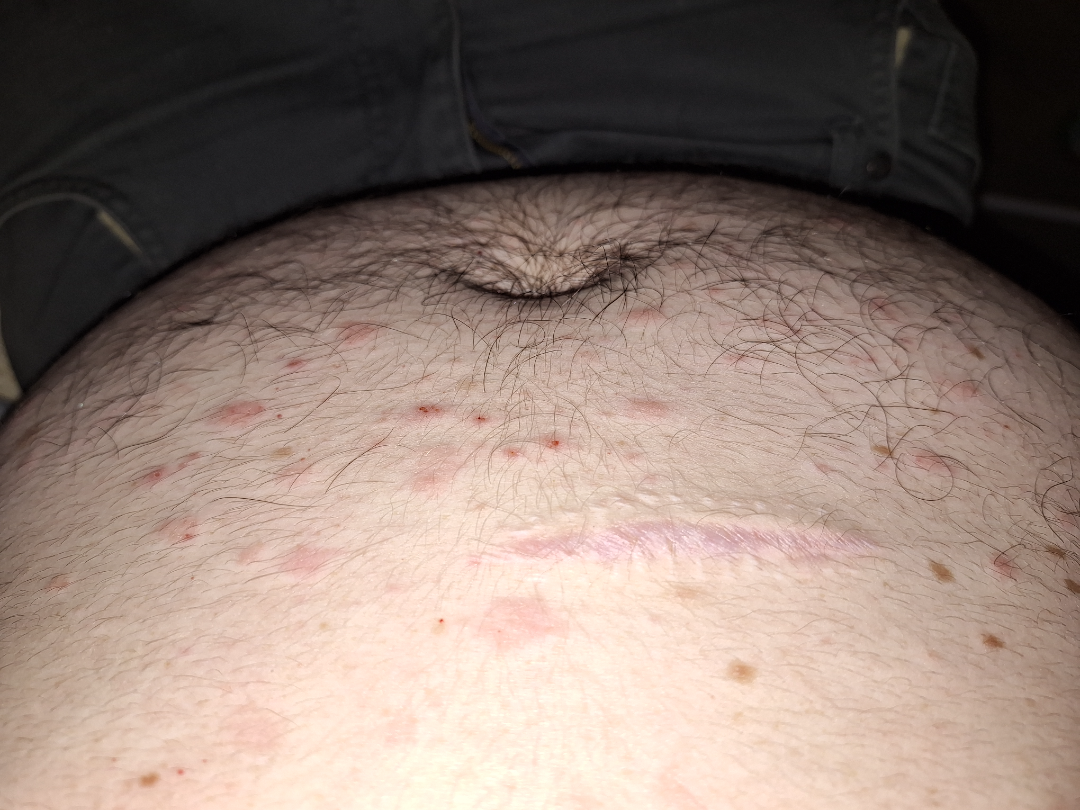Impression: On photographic review by a dermatologist: Pityriasis lichenoides (weight 0.33); Scabies (weight 0.33); Folliculitis (weight 0.33).